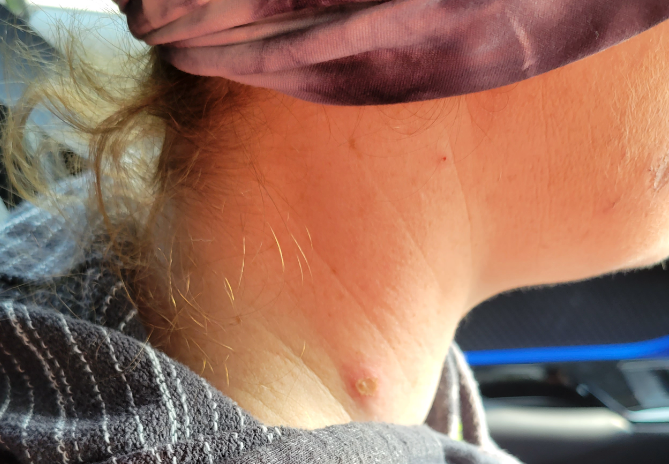assessment: ungradable on photographic review | subject: female, age 30–39 | view: at a distance | anatomic site: head or neck.